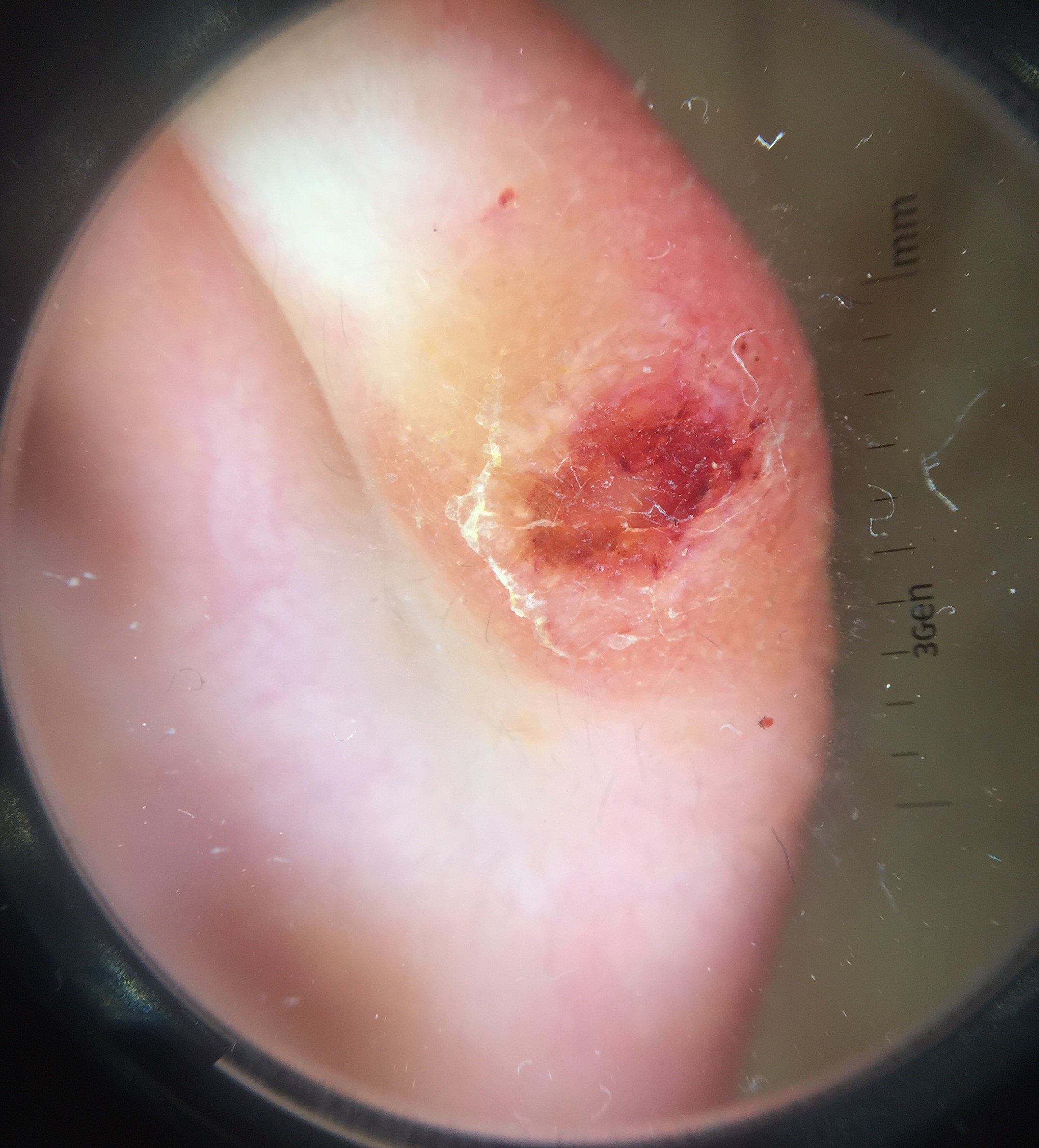<case>
  <image>dermatoscopy</image>
  <lesion_type>
    <main_class>keratinocytic</main_class>
  </lesion_type>
  <diagnosis>
    <name>squamous cell carcinoma</name>
    <code>scc</code>
    <malignancy>malignant</malignancy>
    <super_class>non-melanocytic</super_class>
    <confirmation>histopathology</confirmation>
  </diagnosis>
</case>